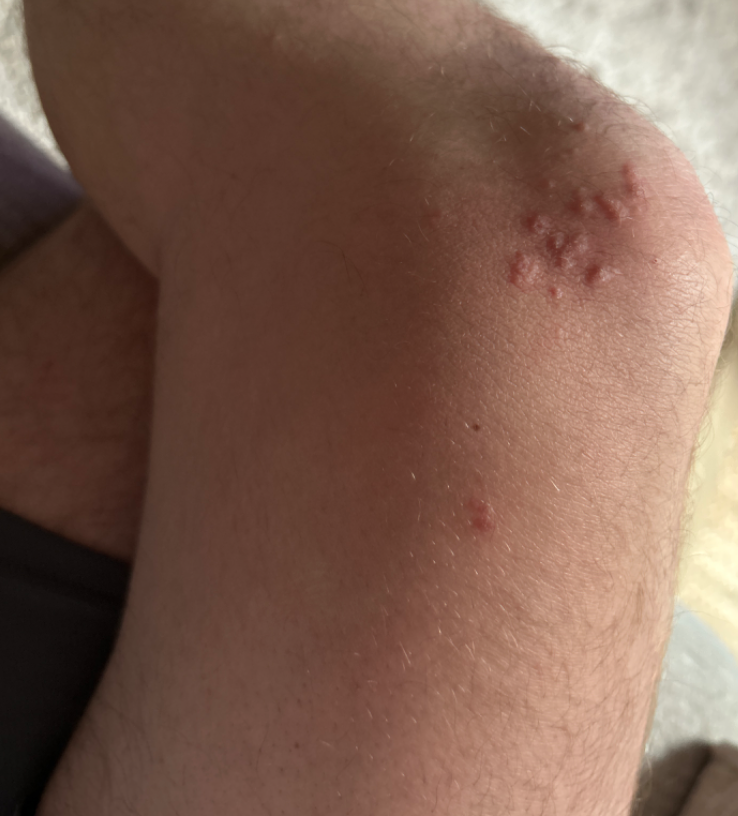The dermatologist could not determine a likely condition from the photograph alone.
Male patient, age 40–49.
The patient described the issue as a rash.
Present for less than one week.
The leg is involved.
Texture is reported as raised or bumpy.
Reported lesion symptoms include itching.
The photograph was taken at a distance.